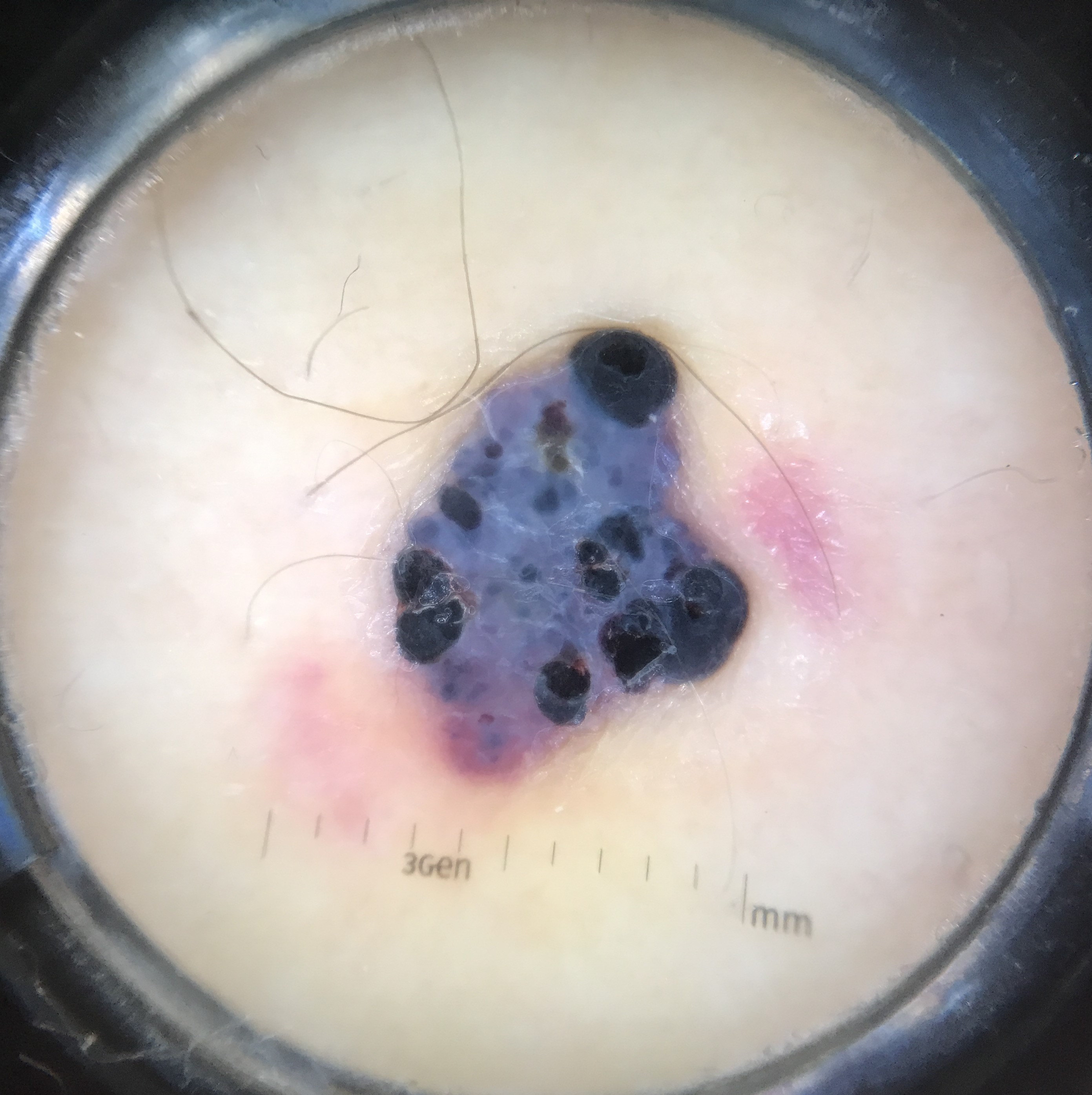label: angiokeratoma (expert consensus).